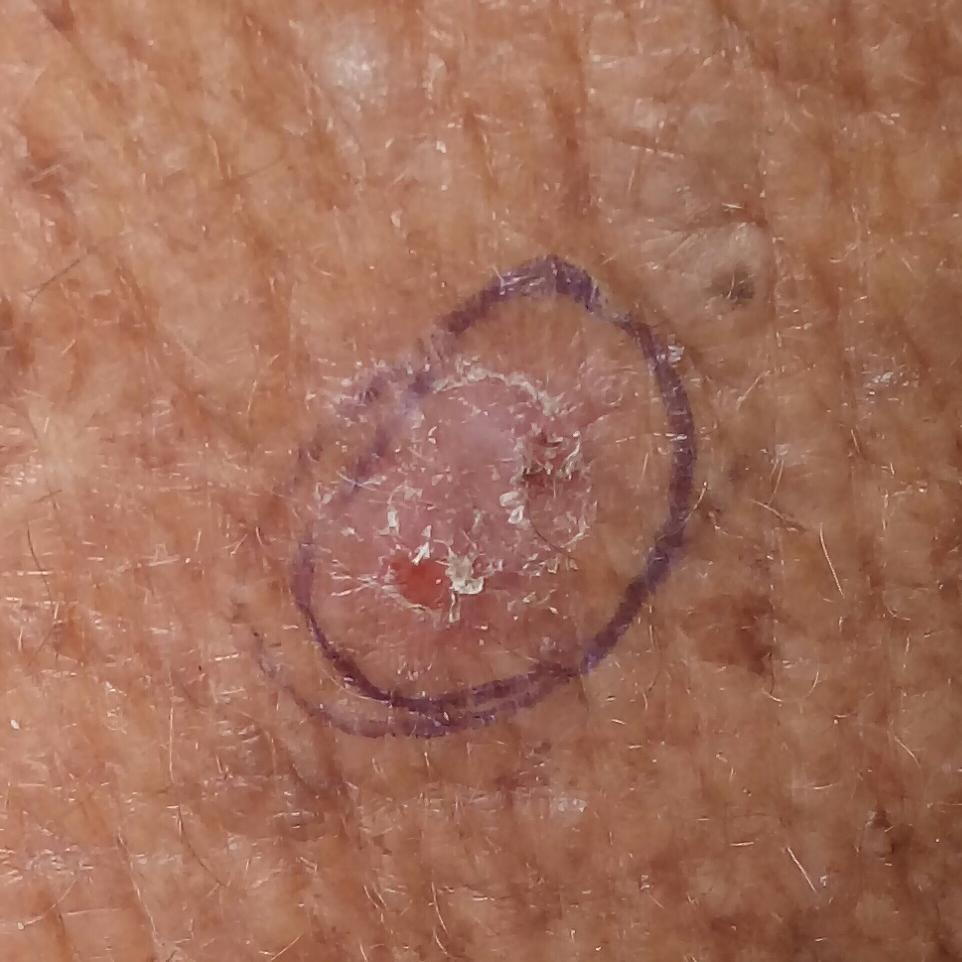subject = in their late 60s; imaging = smartphone clinical photo; location = a forearm; reported symptoms = itching / no elevation; impression = actinic keratosis (clinical consensus).